Close-up view: 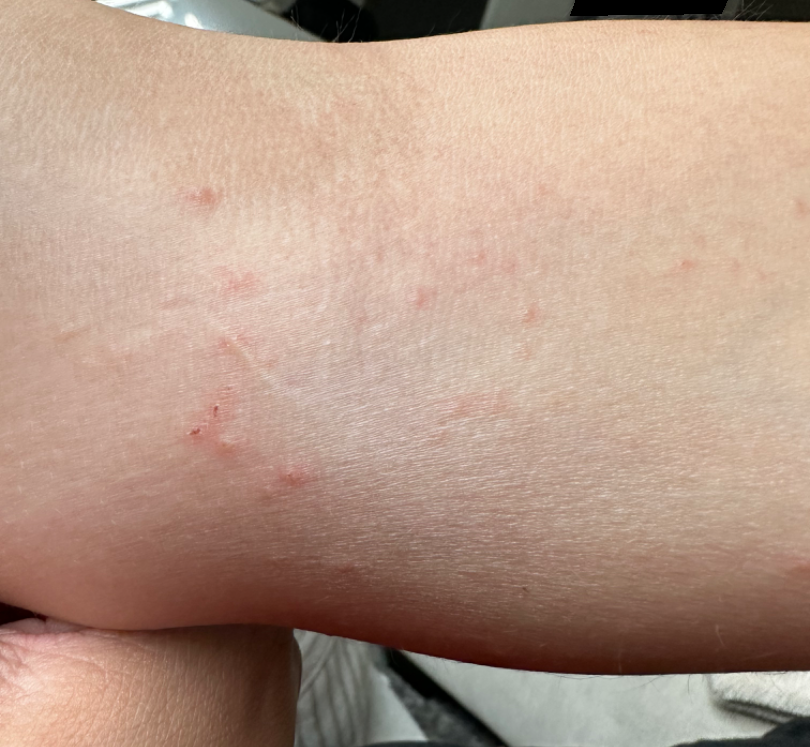Review:
On dermatologist assessment of the image, the primary impression is Allergic Contact Dermatitis; possibly Eczema.